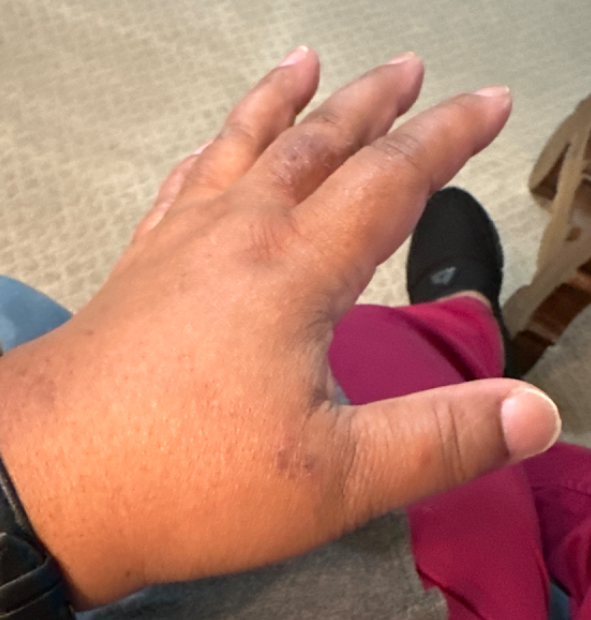The dermatologist could not determine a likely condition from the photograph alone.
Present for less than one week.
The patient notes itching.
The patient considered this a rash.
The back of the hand is involved.
This image was taken at a distance.
The lesion is described as rough or flaky and raised or bumpy.